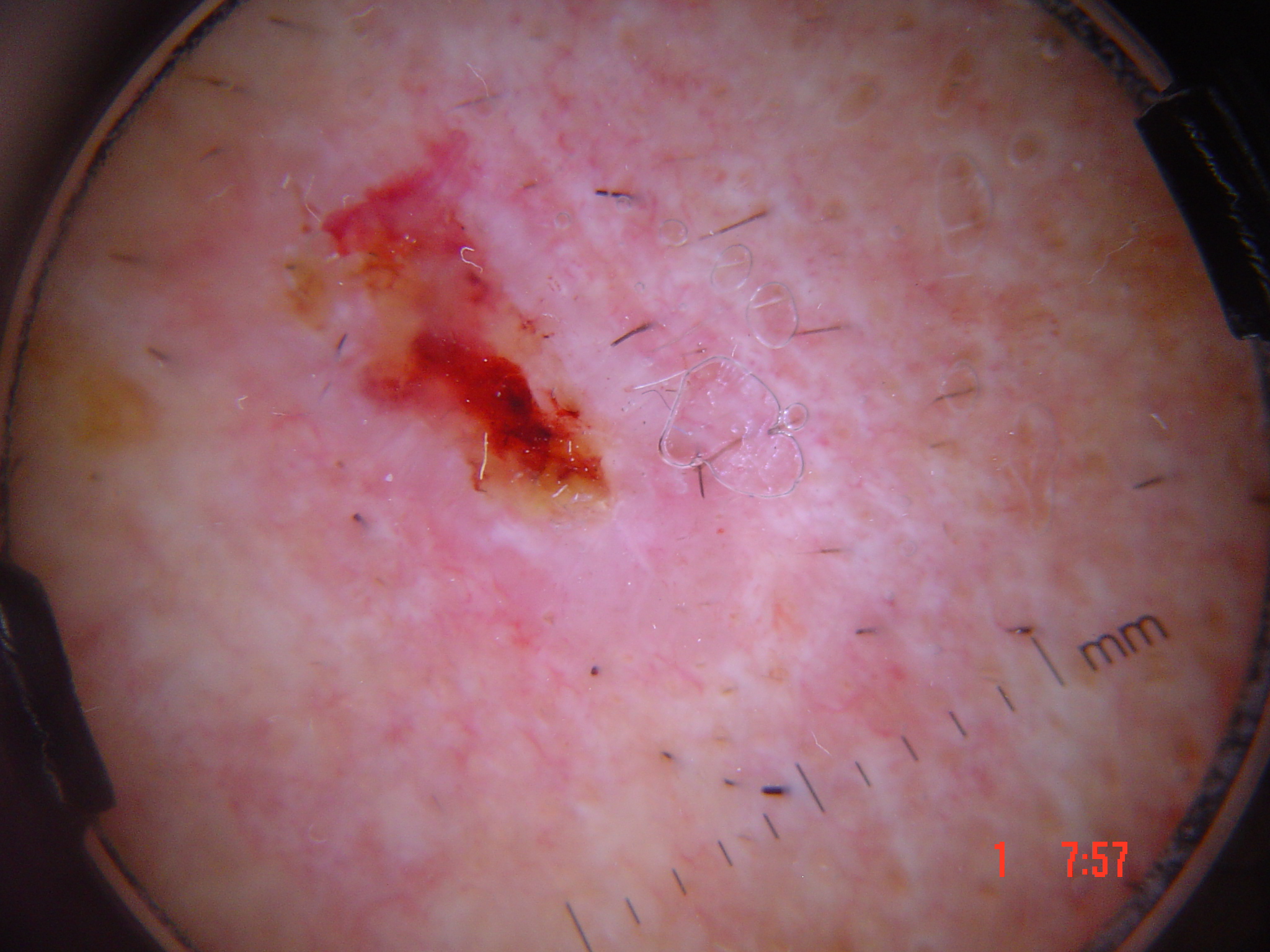Case:
A dermatoscopic image of a skin lesion. The morphology is that of a keratinocytic lesion.
Pathology:
The biopsy diagnosis was a malignant lesion — a squamous cell carcinoma.